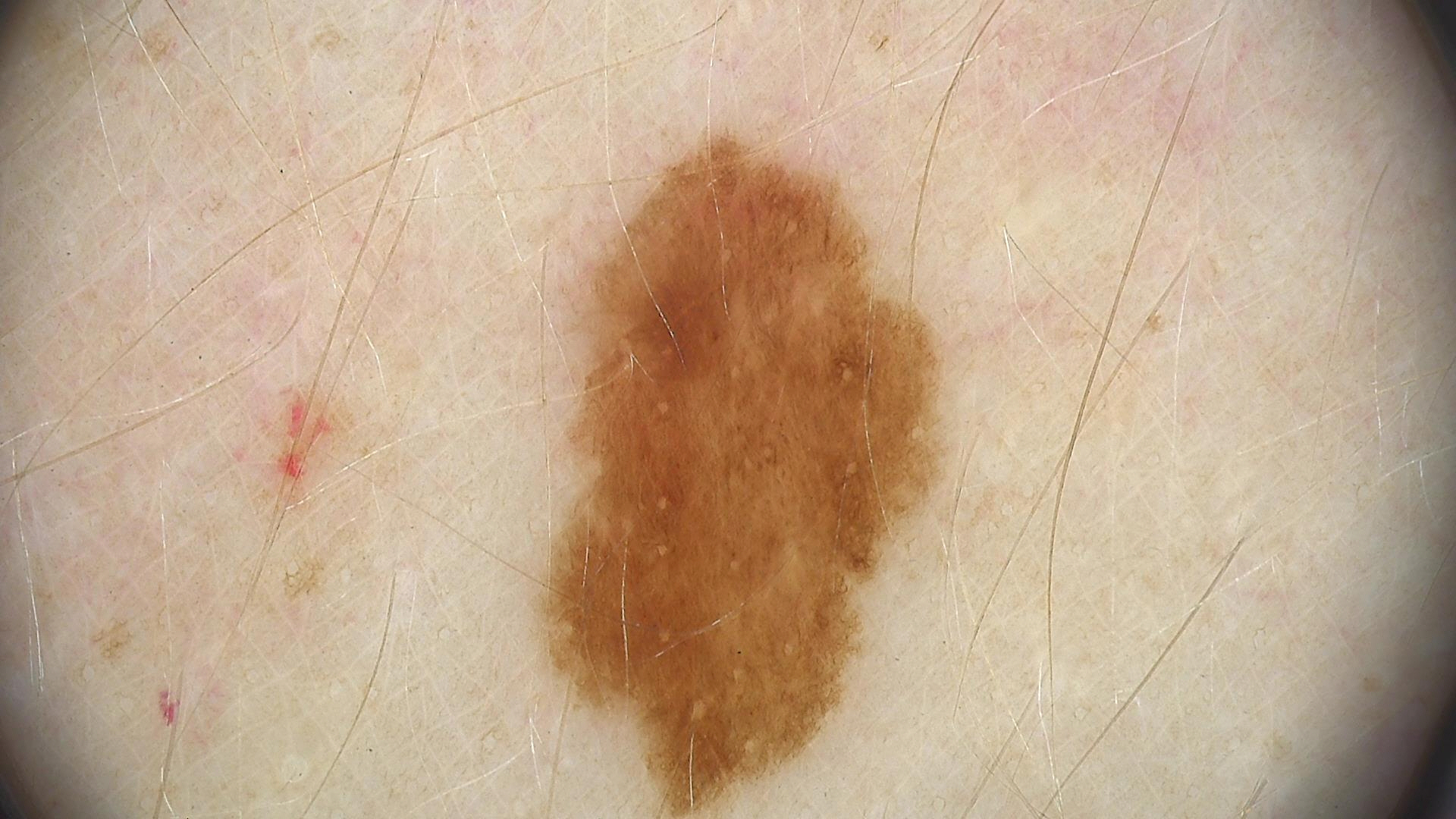| key | value |
|---|---|
| diagnosis | dysplastic junctional nevus (expert consensus) |